An image taken at a distance — 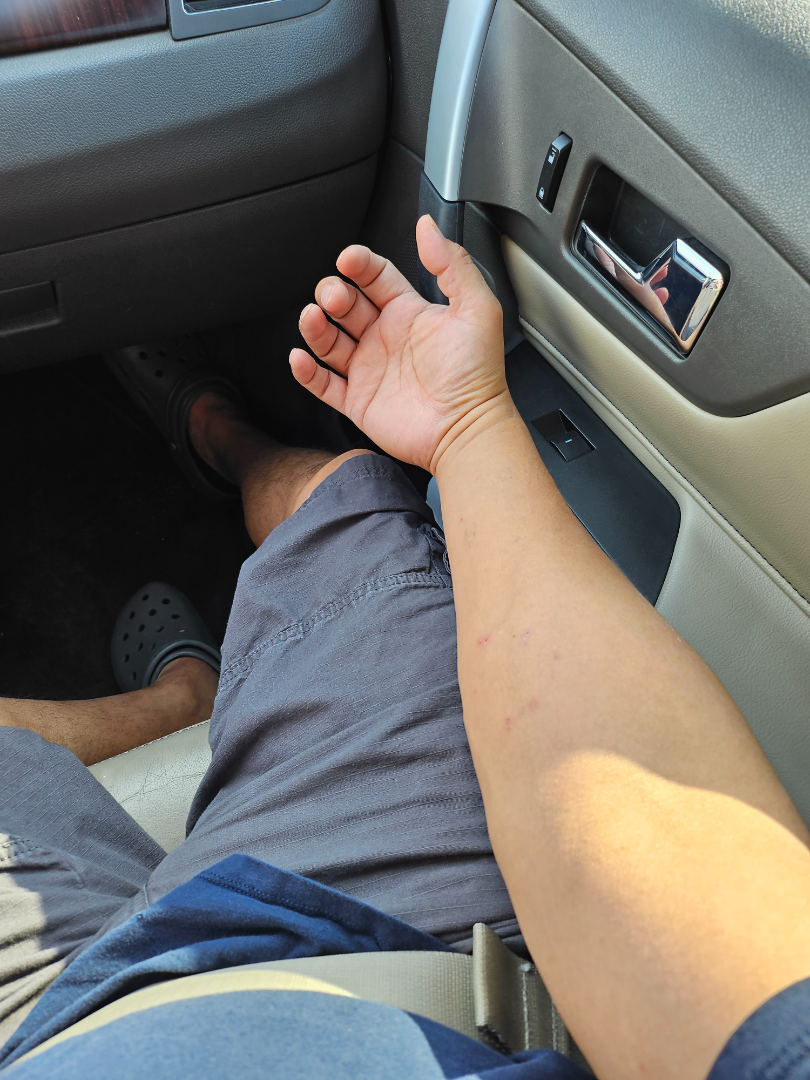impression — most consistent with Lichen planus/lichenoid eruption; an alternative is Eczema; also consider Insect Bite.